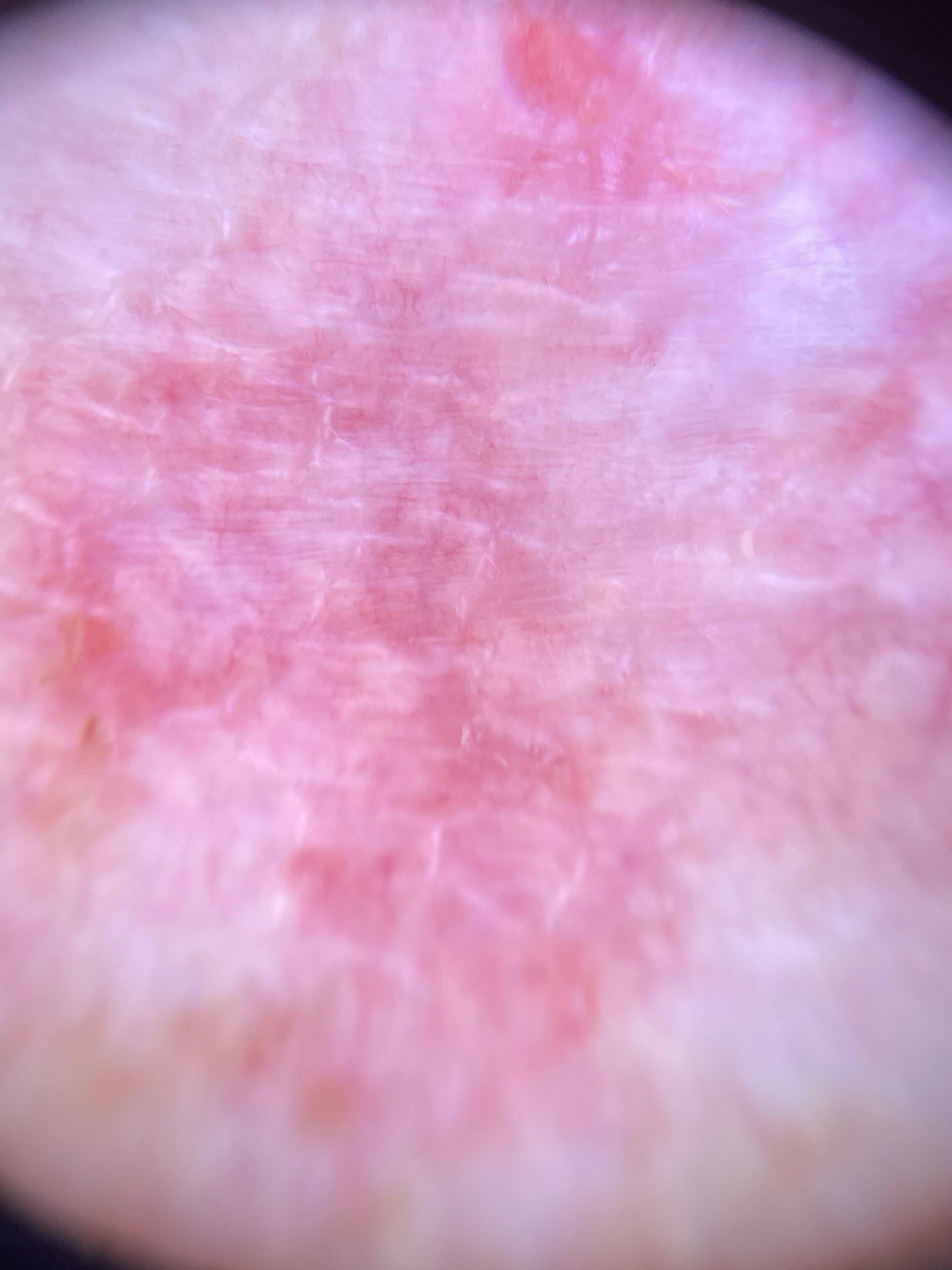<case>
  <skin_type>I</skin_type>
  <patient>
    <age_approx>80</age_approx>
    <sex>female</sex>
  </patient>
  <lesion_location>
    <region>the trunk</region>
    <detail>the anterior trunk</detail>
  </lesion_location>
  <diagnosis>
    <name>Basal cell carcinoma</name>
    <malignancy>malignant</malignancy>
    <confirmation>histopathology</confirmation>
    <lineage>adnexal</lineage>
  </diagnosis>
</case>